A male patient age 66. A clinical photograph showing a skin lesion. Imaged for a research study, with no referral diagnosis recorded.
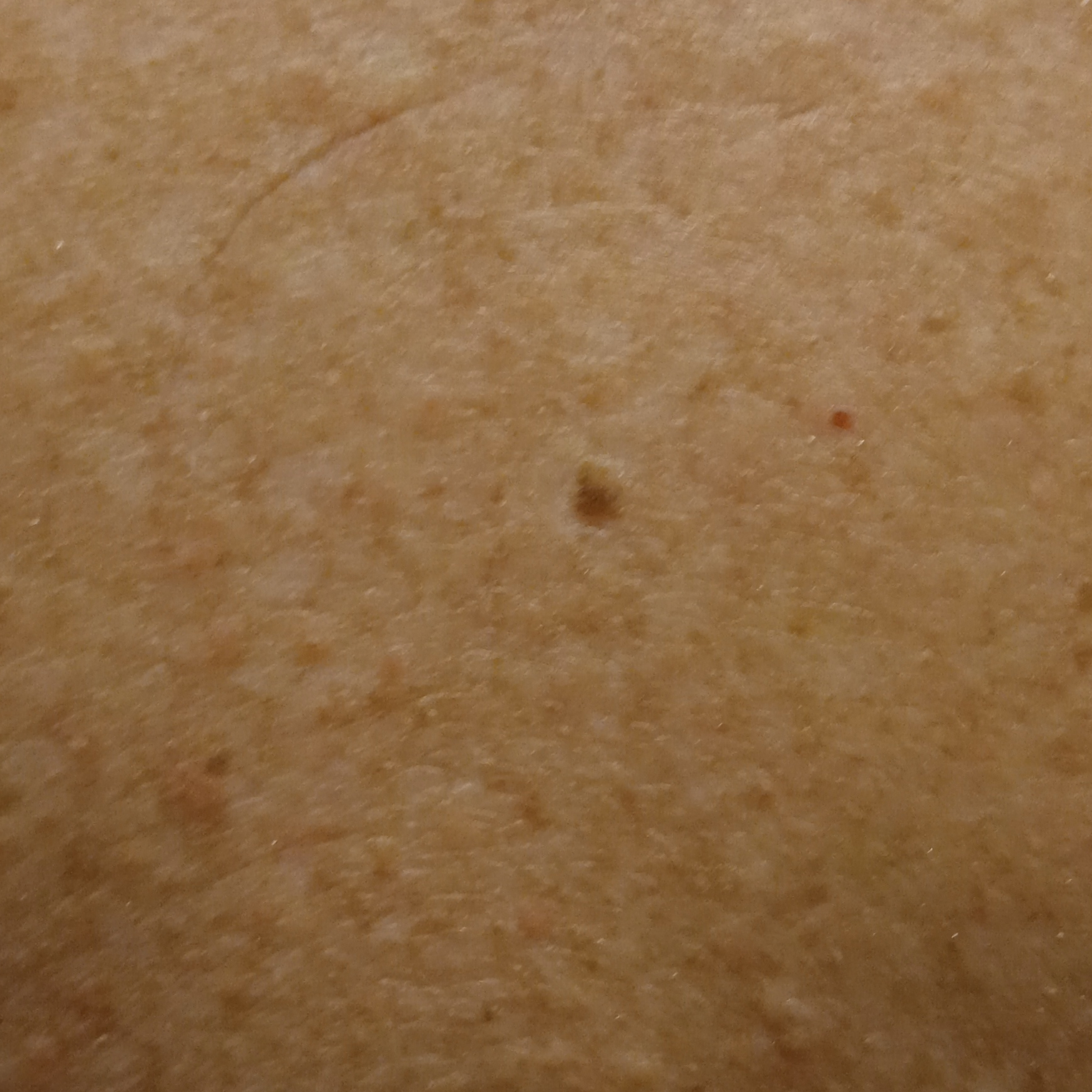Q: Where is the lesion?
A: the back
Q: How large is the lesion?
A: 4.5 mm
Q: What was the diagnosis?
A: seborrheic keratosis (dermatologist consensus)